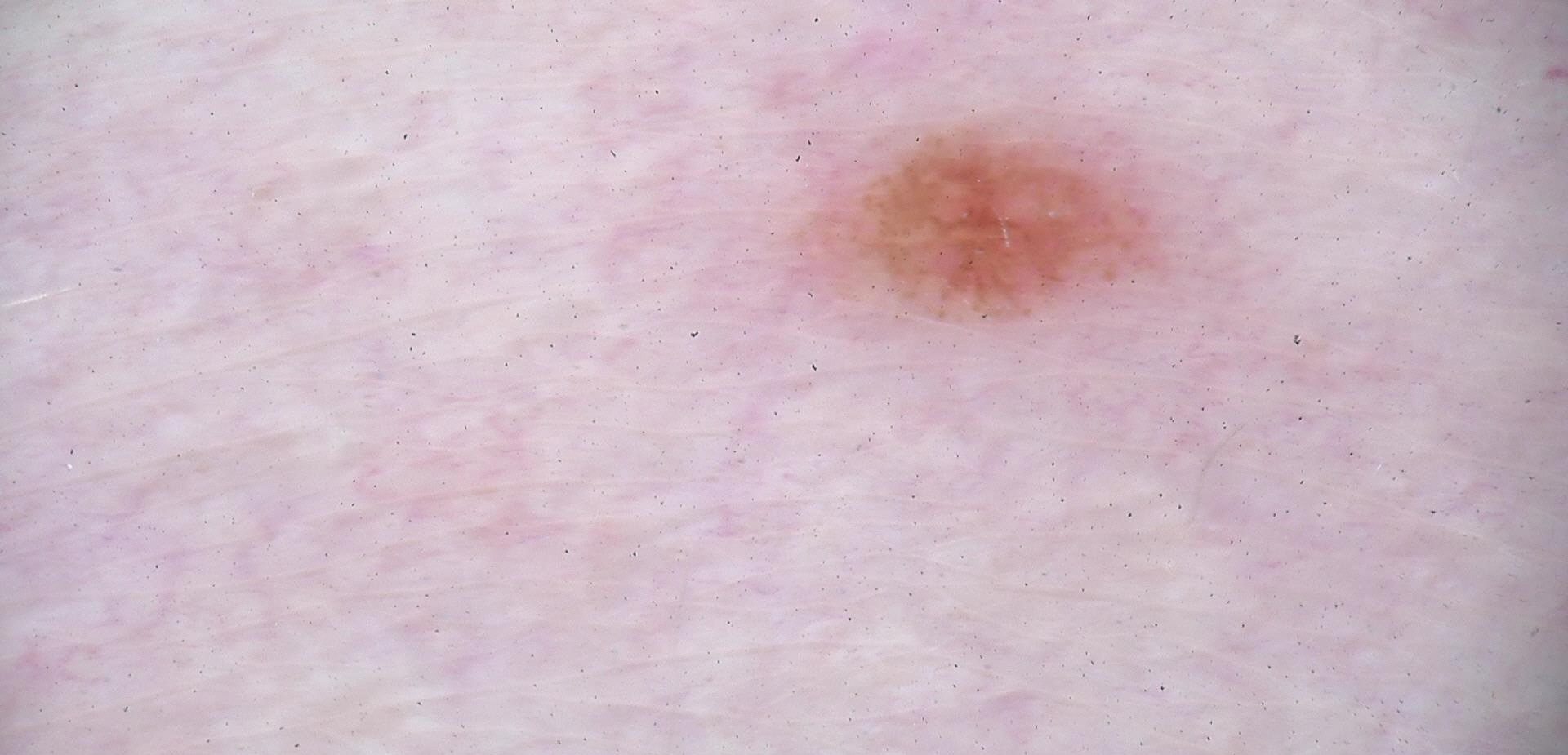A dermoscopic photograph of a skin lesion.
Labeled as a benign lesion — a dysplastic junctional nevus.